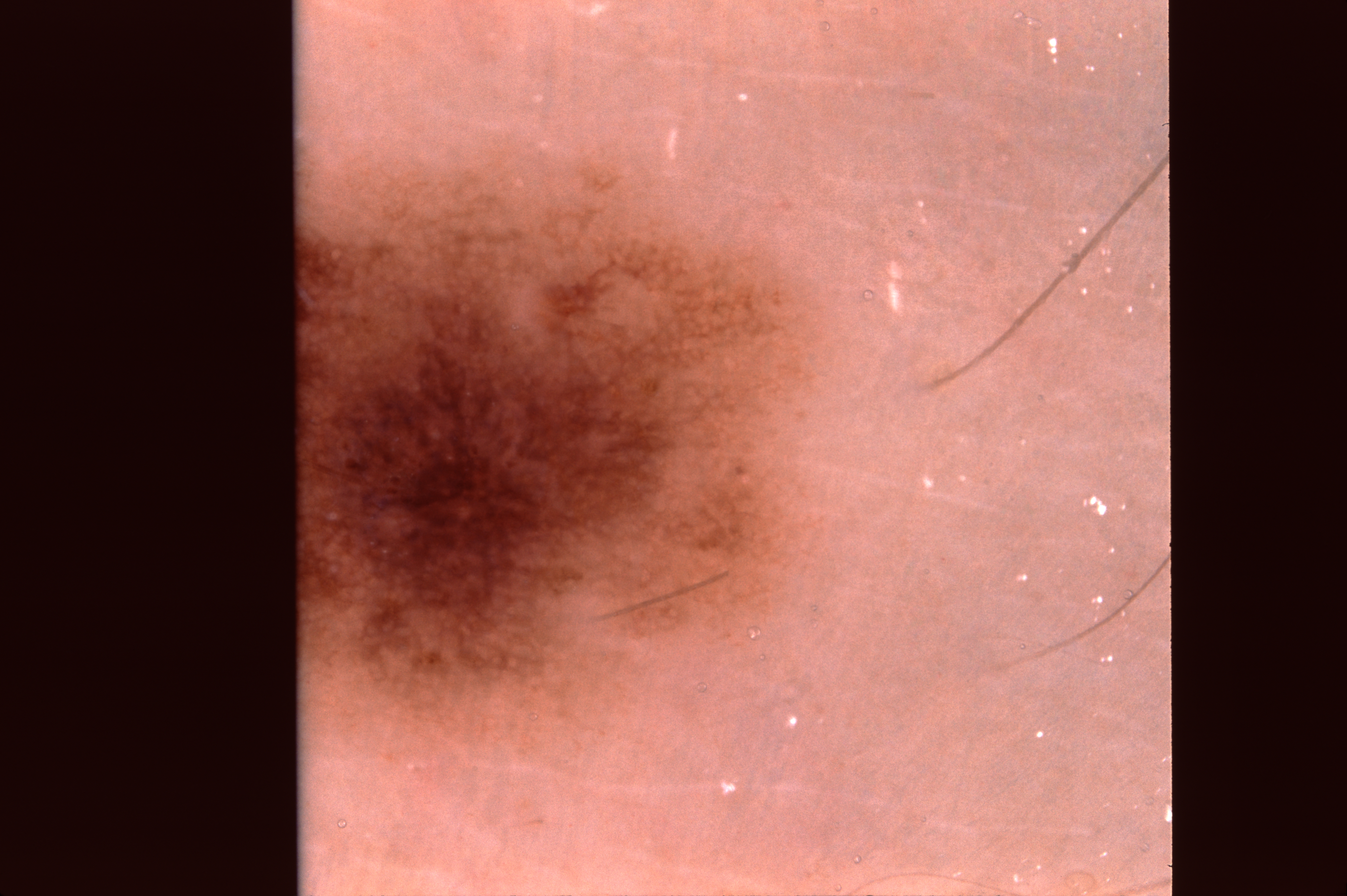A female subject, approximately 30 years of age. This is a dermoscopic photograph of a skin lesion. Dermoscopic assessment notes pigment network; no negative network, milia-like cysts, or streaks. The lesion spans x1=291, y1=0, x2=823, y2=895. Consistent with a melanocytic nevus, a benign lesion.